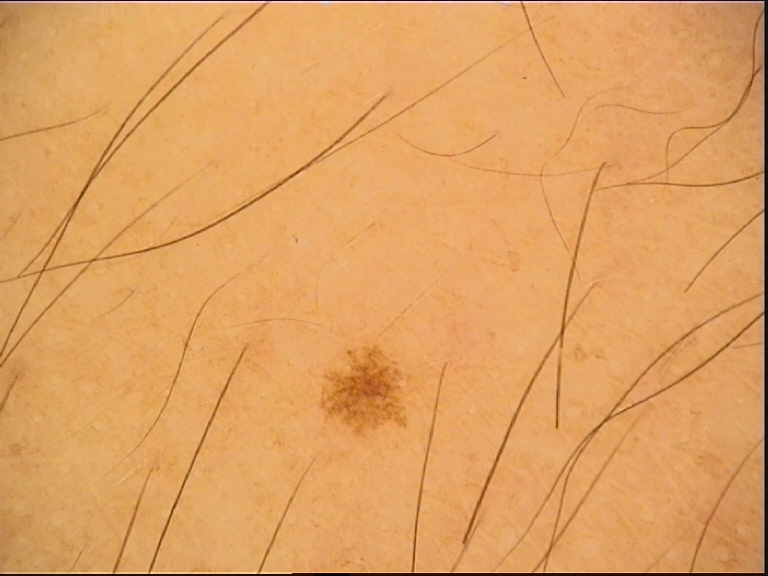diagnostic label: dysplastic junctional nevus (expert consensus).